A female subject aged 67; a clinical close-up of a skin lesion; the patient reports a personal history of skin cancer.
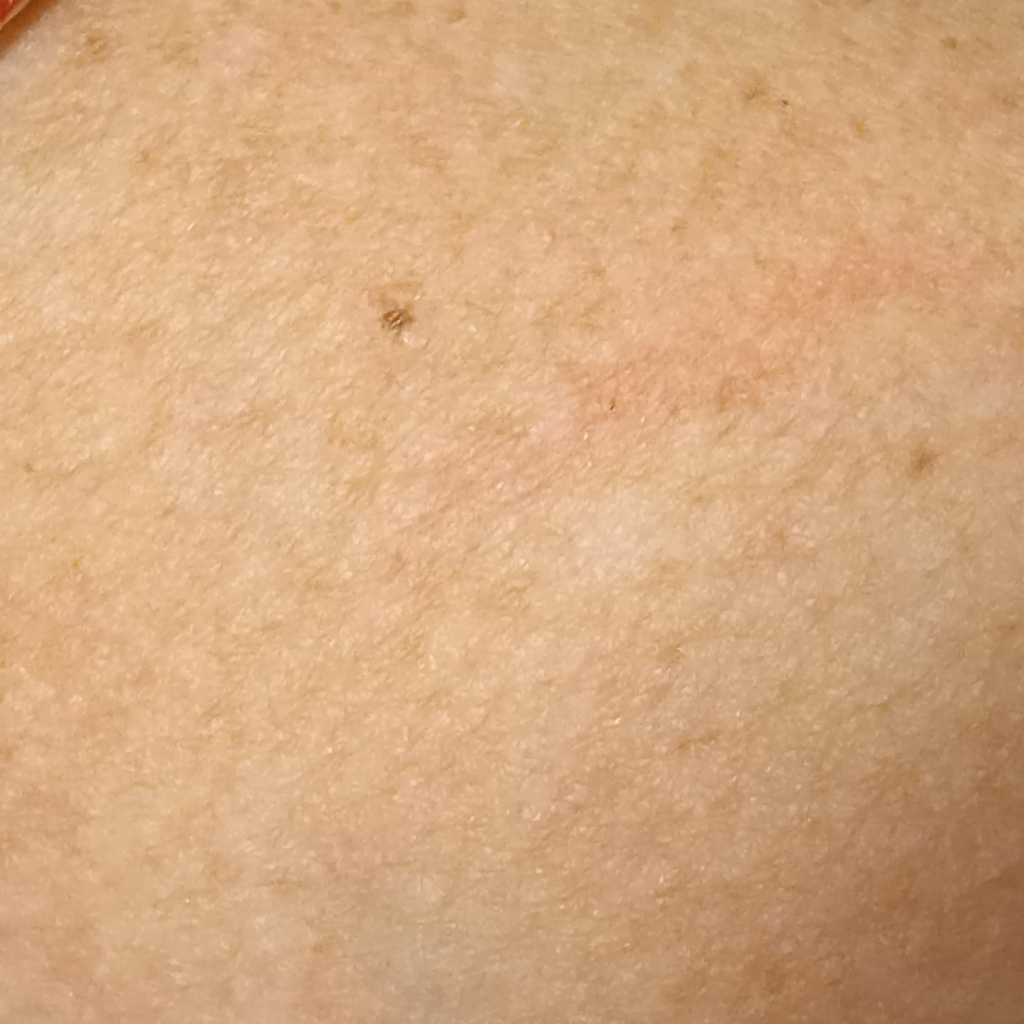Located on an arm. The lesion is about 1.3 mm across. Dermatologist review favored a melanocytic nevus.